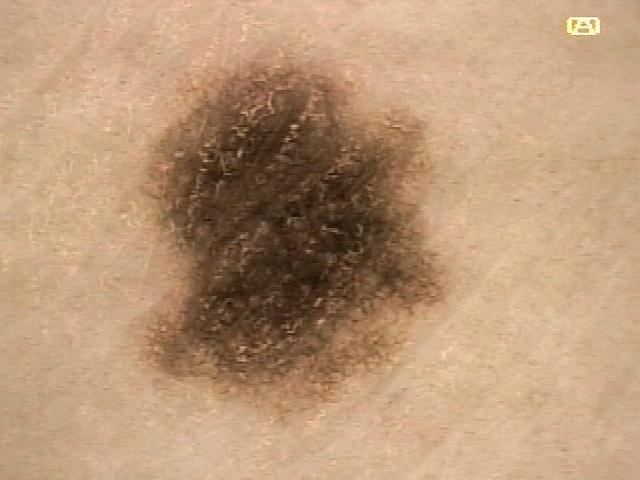modality — contact-polarized dermoscopy; patient — female, aged 48-52; Fitzpatrick — I; anatomic site — a lower extremity; diagnostic label — Nevus (biopsy-proven).